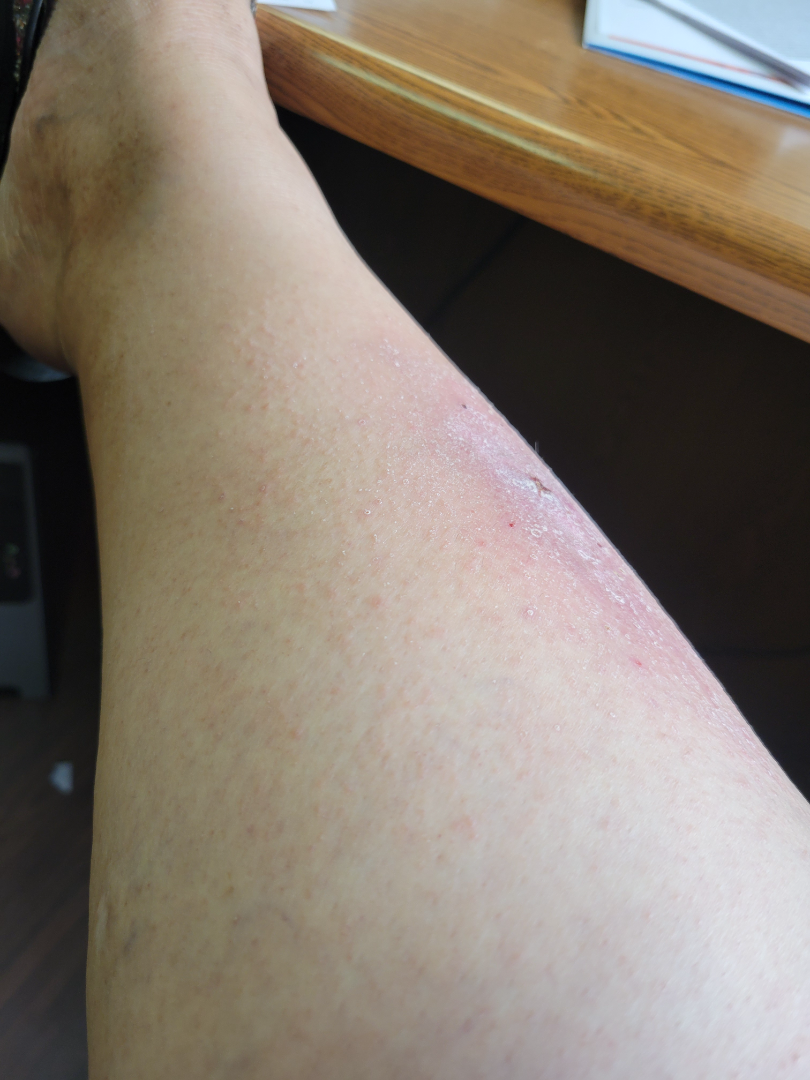The photo was captured at an angle. The affected area is the leg. One reviewing dermatologist: the leading impression is Eczema; also consider Psoriasis; also raised was Allergic Contact Dermatitis.